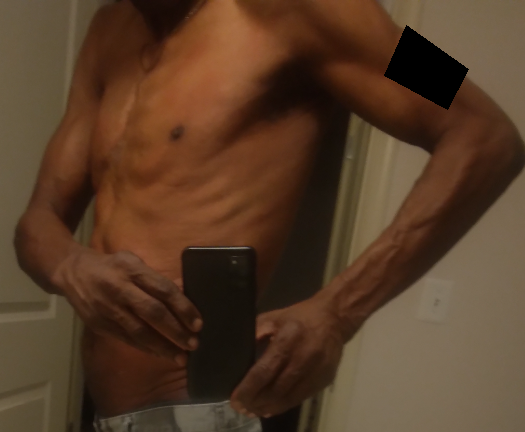Diagnostic features were not clearly distinguishable in this photograph.